Imaged for a research study, with no referral diagnosis recorded · a dermoscopic image of a skin lesion · a female subject aged 81 — 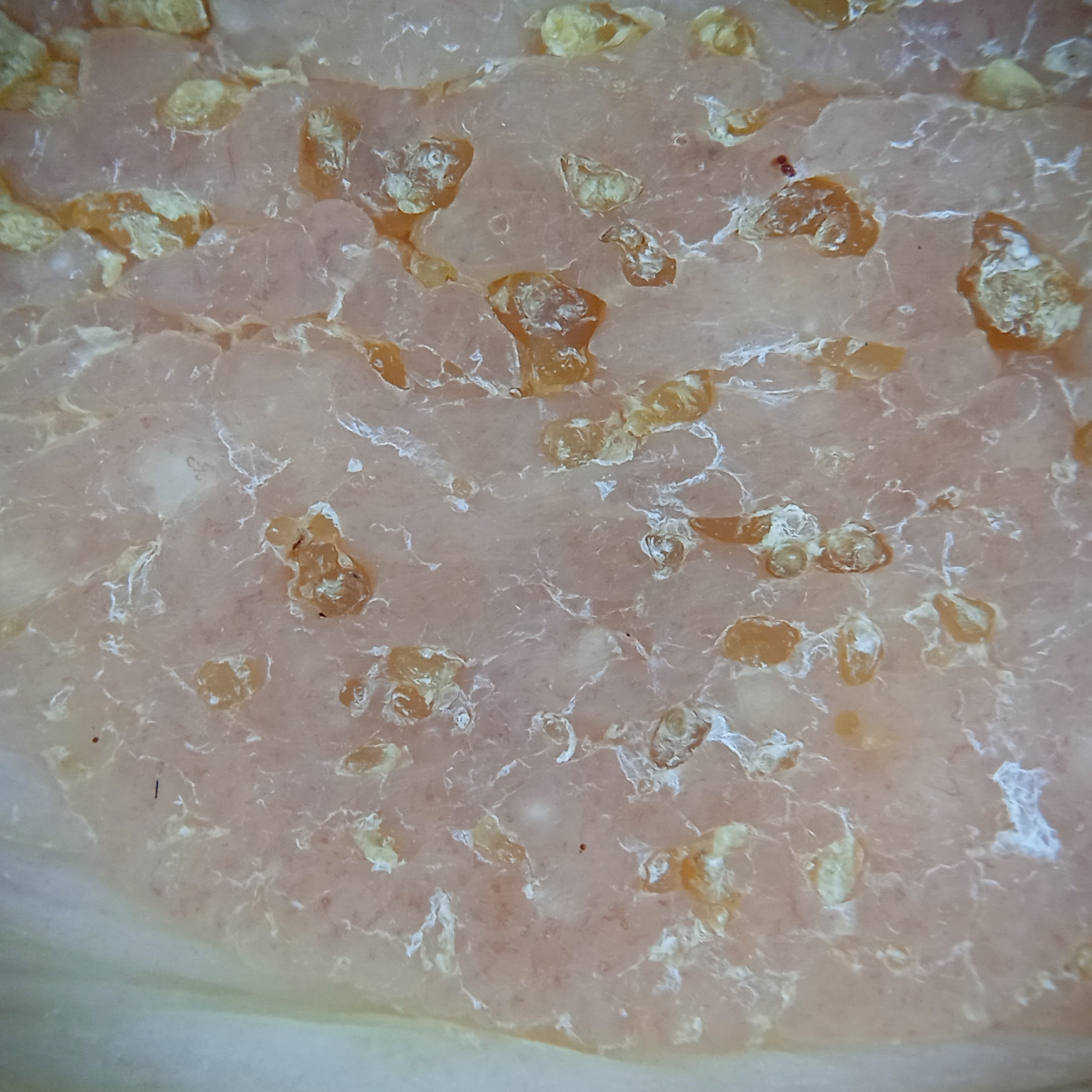<skin_lesion>
  <lesion_location>the torso</lesion_location>
  <lesion_size>
    <diameter_mm>31.0</diameter_mm>
  </lesion_size>
  <diagnosis>
    <name>seborrheic keratosis</name>
    <malignancy>benign</malignancy>
    <certainty>good</certainty>
  </diagnosis>
</skin_lesion>